A male subject aged approximately 80, a dermoscopy image of a single skin lesion: 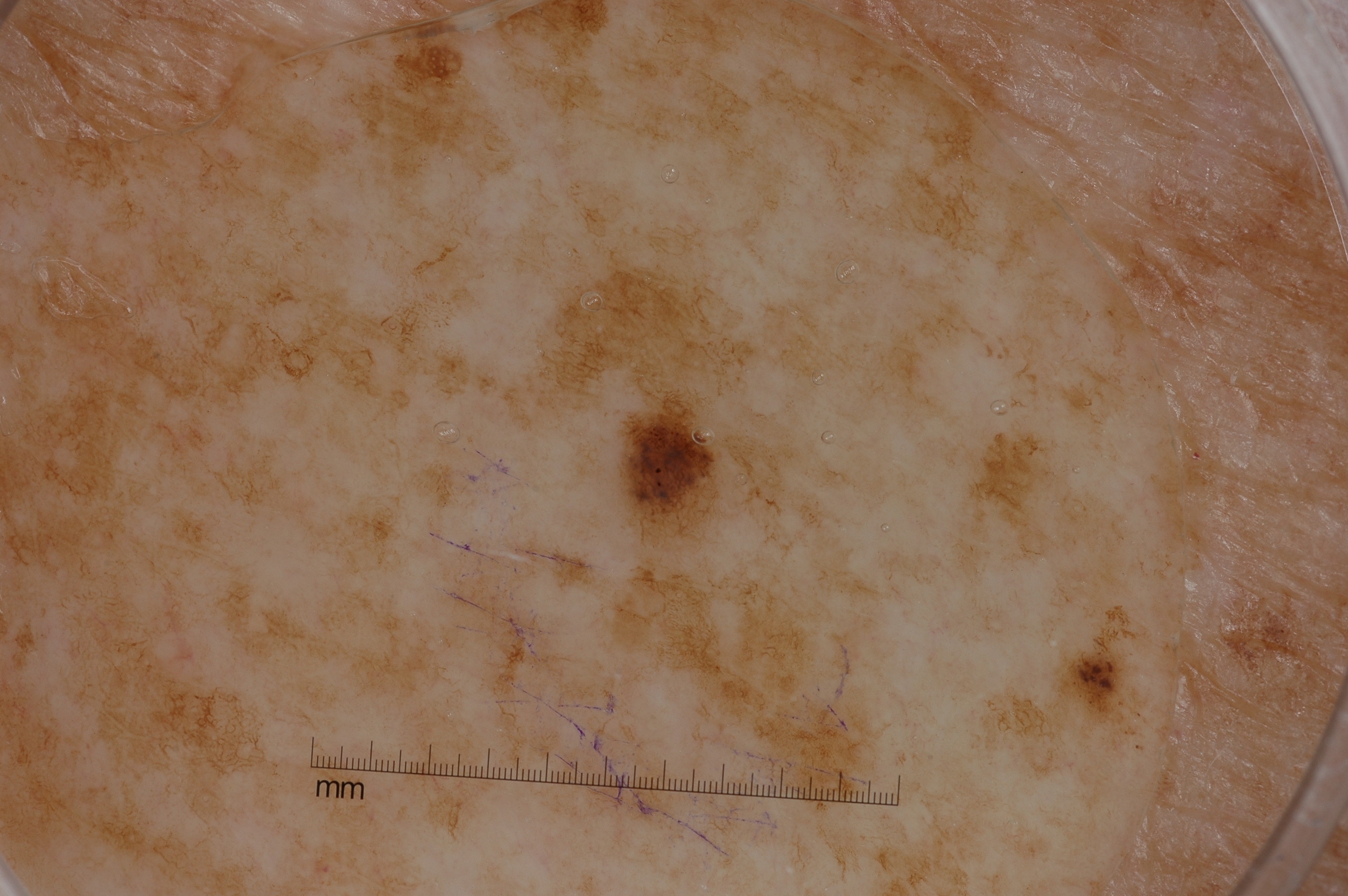  dermoscopic_features:
    present:
      - pigment network
    absent:
      - streaks
      - milia-like cysts
      - negative network
  lesion_location:
    bbox_xyxy:
      - 612
      - 382
      - 741
      - 561
  diagnosis:
    name: melanocytic nevus
    malignancy: benign
    lineage: melanocytic
    provenance: clinical